A dermoscopic close-up of a skin lesion.
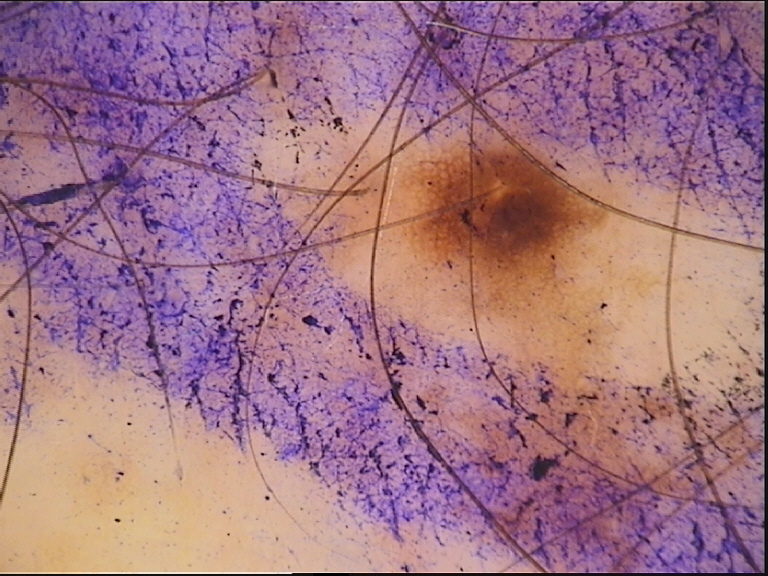assessment=junctional nevus (expert consensus).